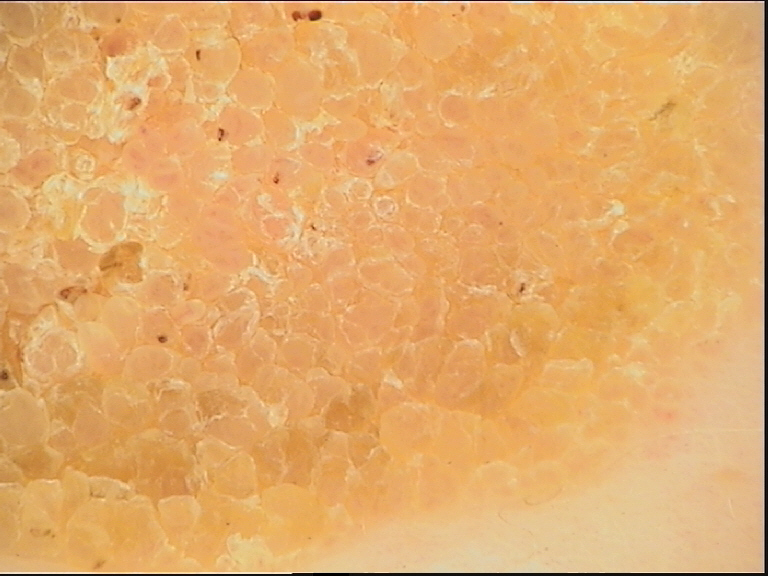modality=dermoscopy
diagnostic label=seborrheic keratosis (expert consensus)